On a questionnaire the patient reported a prior organ transplant. The patient says their skin reddens with sun exposure. The patient describes having few moles overall. A male patient 66 years old:
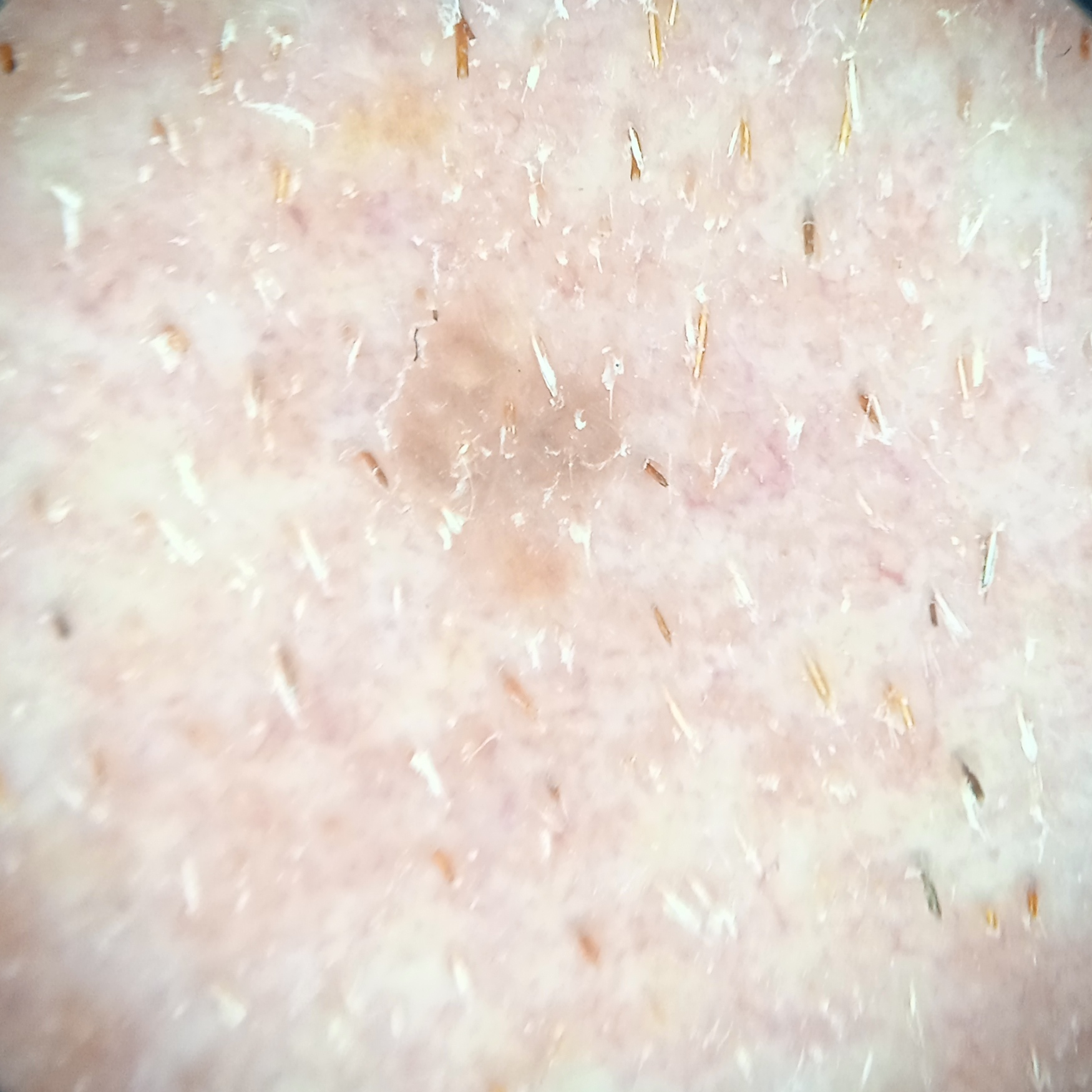Measuring roughly 3 mm. The diagnostic impression was a seborrheic keratosis.